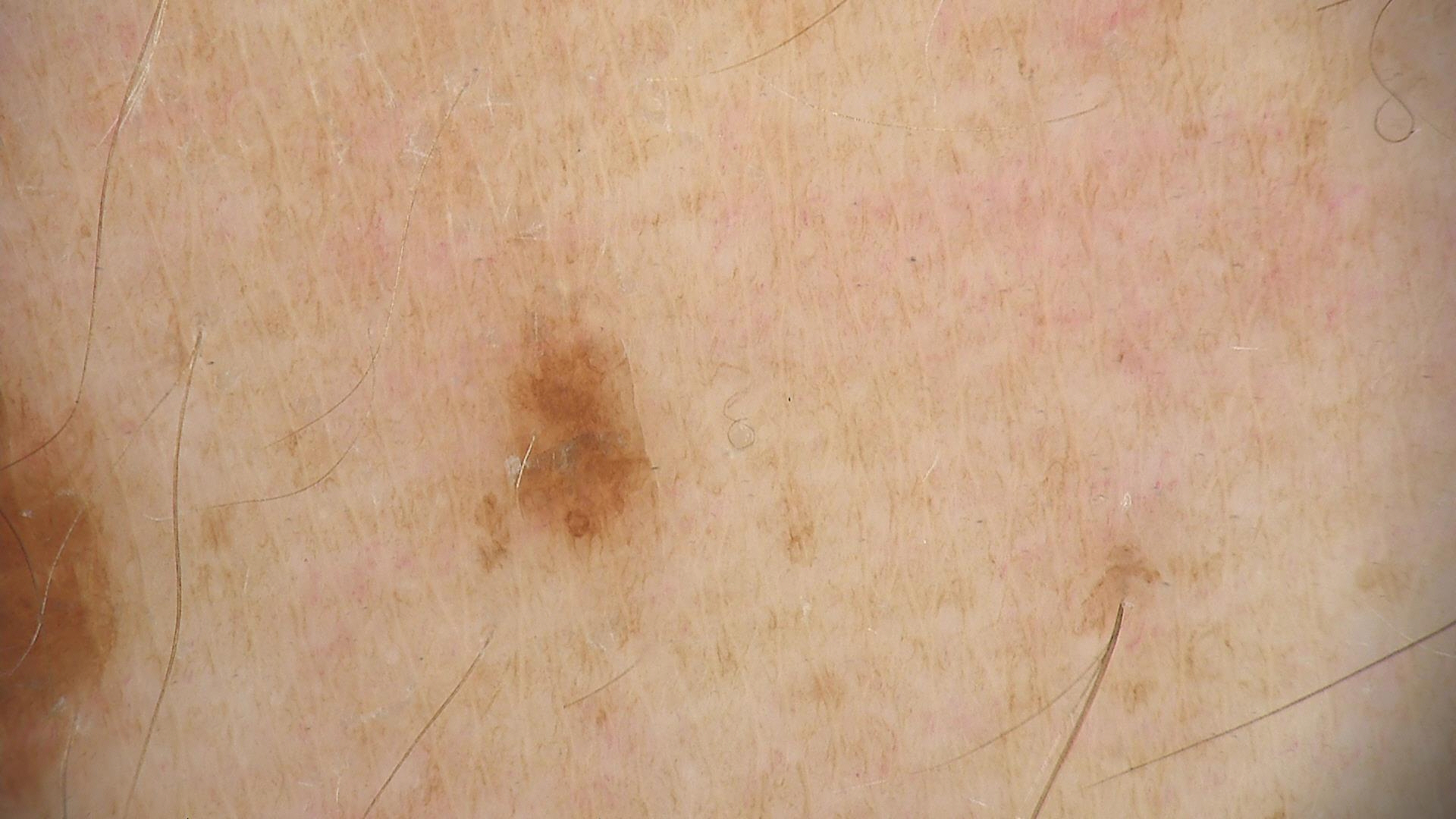A dermoscopic close-up of a skin lesion. The diagnostic label was a dysplastic junctional nevus.